A dermatoscopic image of a skin lesion.
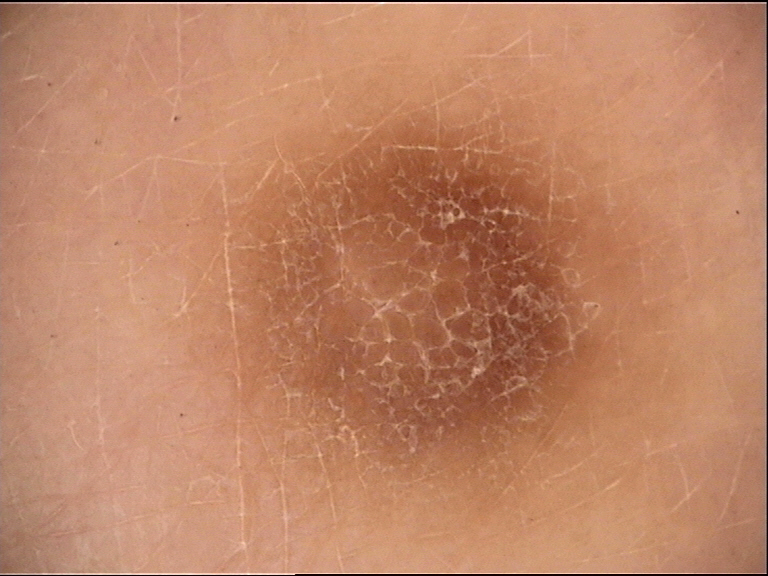Findings: The morphology is that of a fibro-histiocytic lesion. Impression: The diagnostic label was a dermatofibroma.